A patient aged 92; a clinical photo of a skin lesion taken with a smartphone.
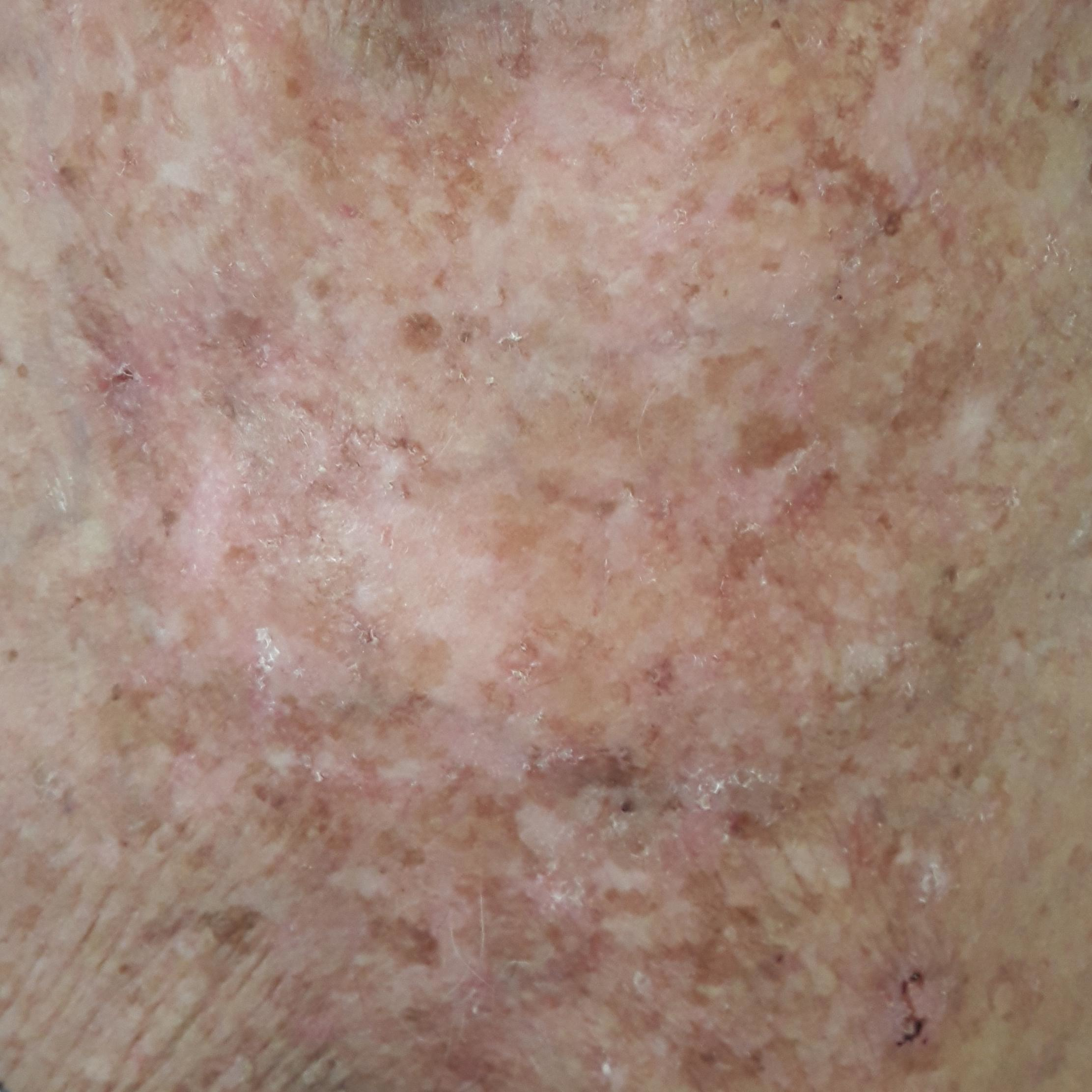Located on the chest.
By the patient's account, the lesion itches.
Clinically diagnosed as a lesion with uncertain malignant potential — an actinic keratosis.